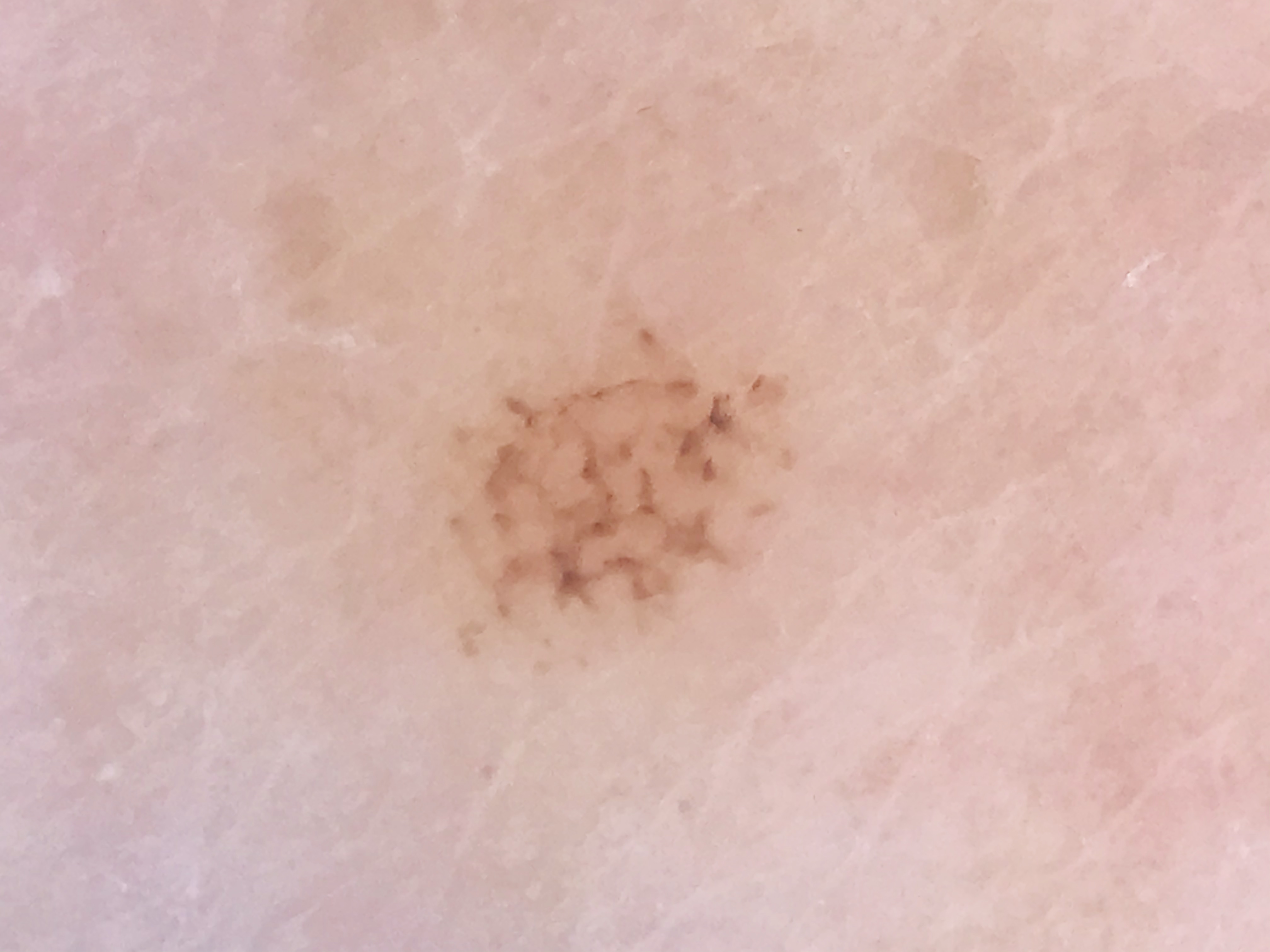modality: dermoscopy
diagnosis: acral dysplastic junctional nevus (expert consensus)